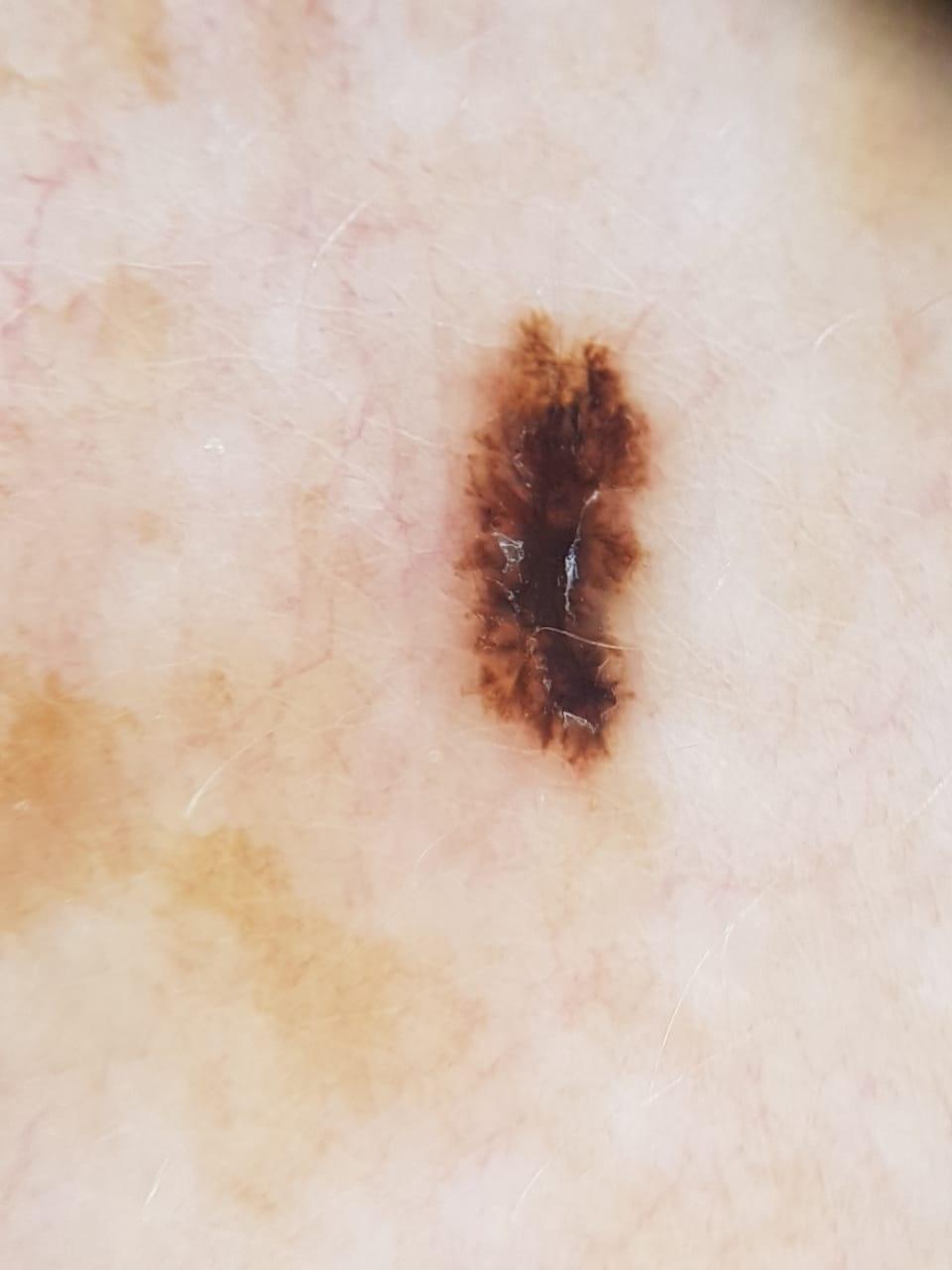Contact-polarized dermoscopy of a skin lesion. A female patient about 60 years old. The lesion is on the trunk. Histopathology confirmed a melanoma.